The photo was captured at an angle · located on the head or neck, front of the torso and back of the torso: 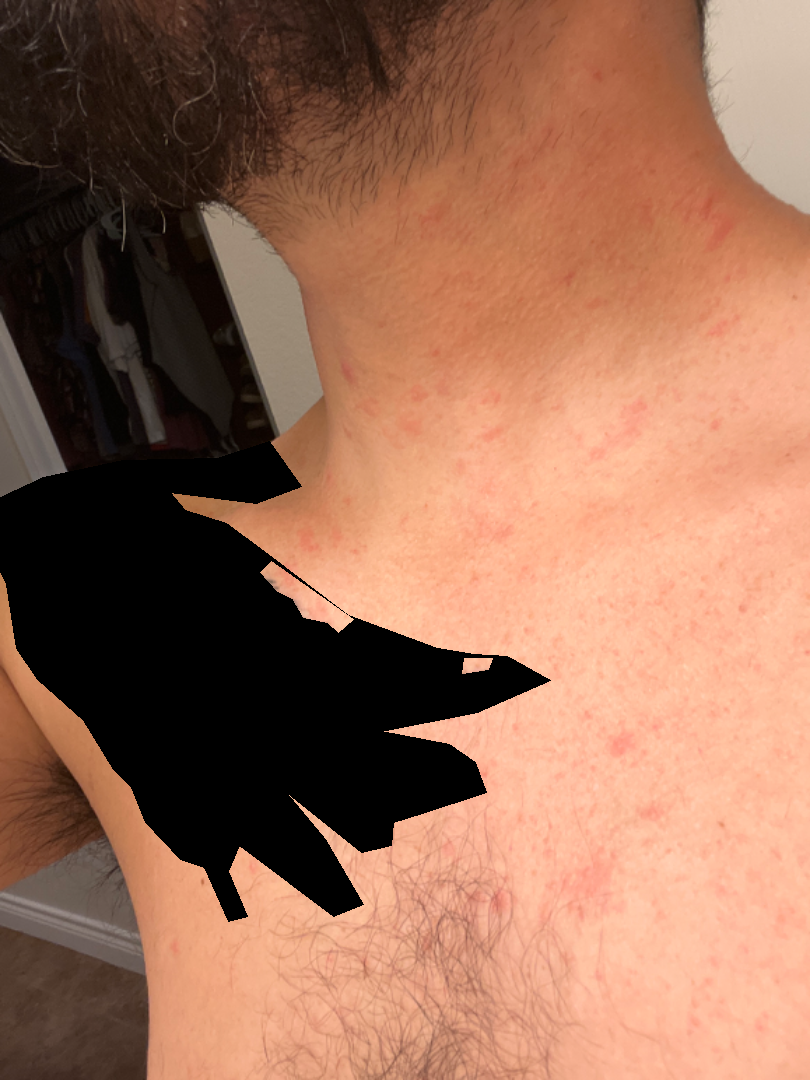Findings: The reviewing dermatologist's impression was: Acute dermatitis (possible); Itchy skin eruption (possible); Viral Exanthem (less likely).